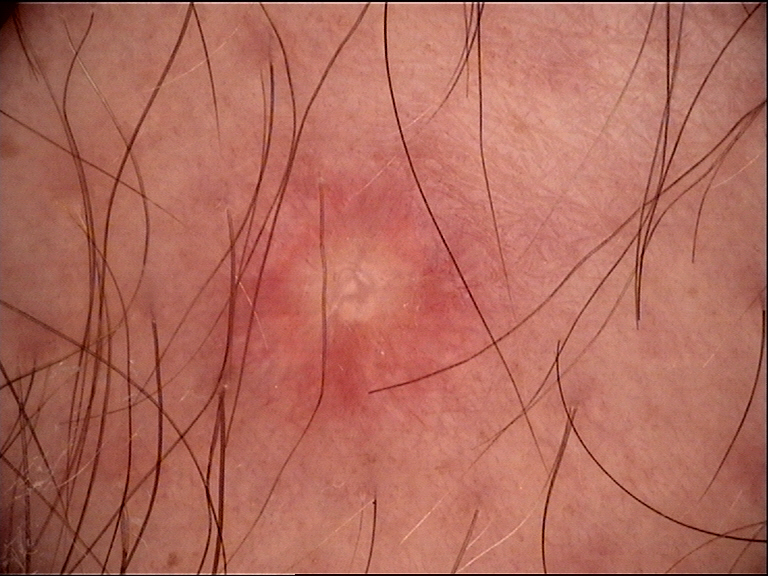| field | value |
|---|---|
| diagnosis | dermatofibroma (expert consensus) |